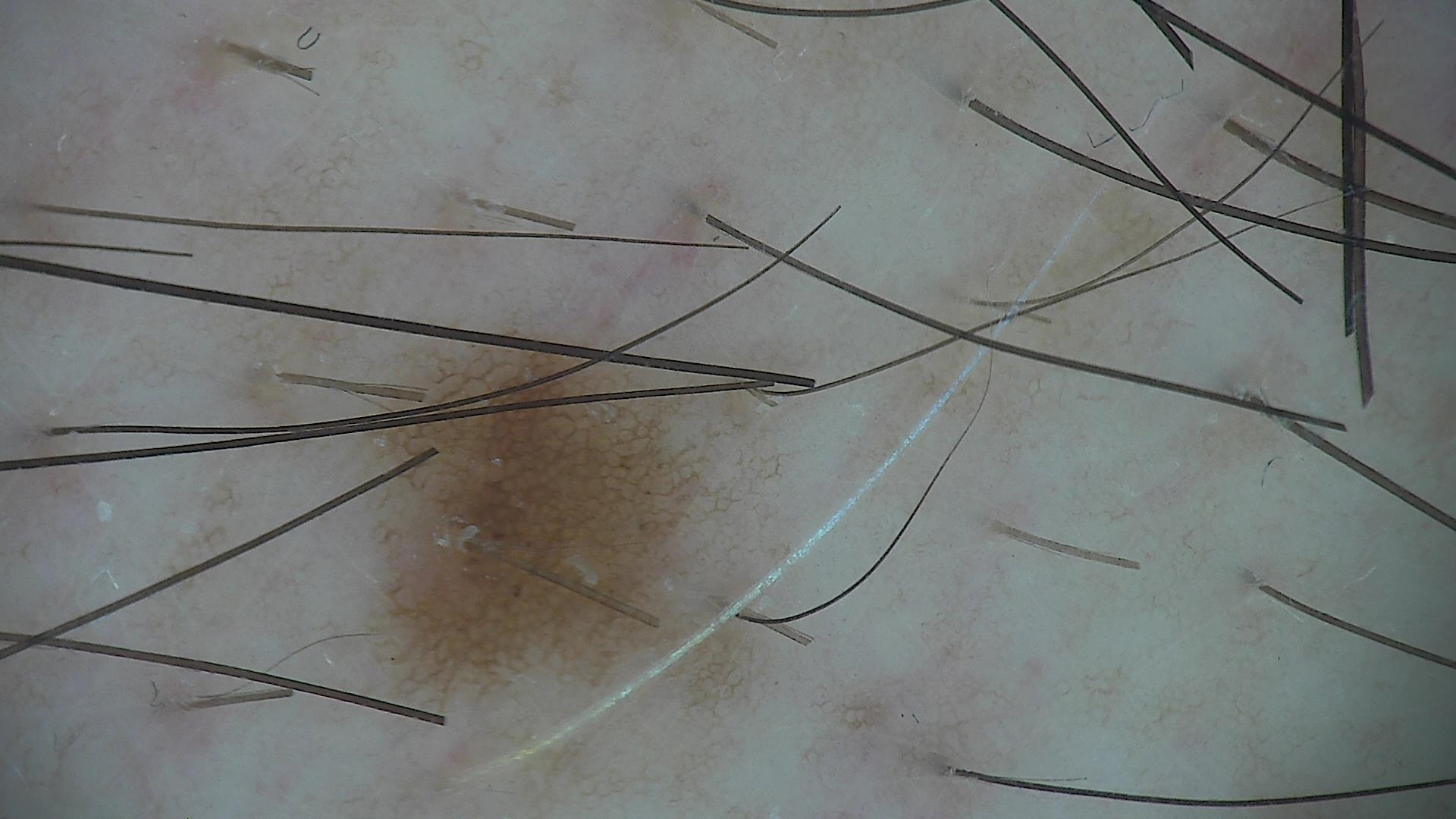class: dysplastic junctional nevus (expert consensus)